Close-up view · the contributor is 18–29, female.
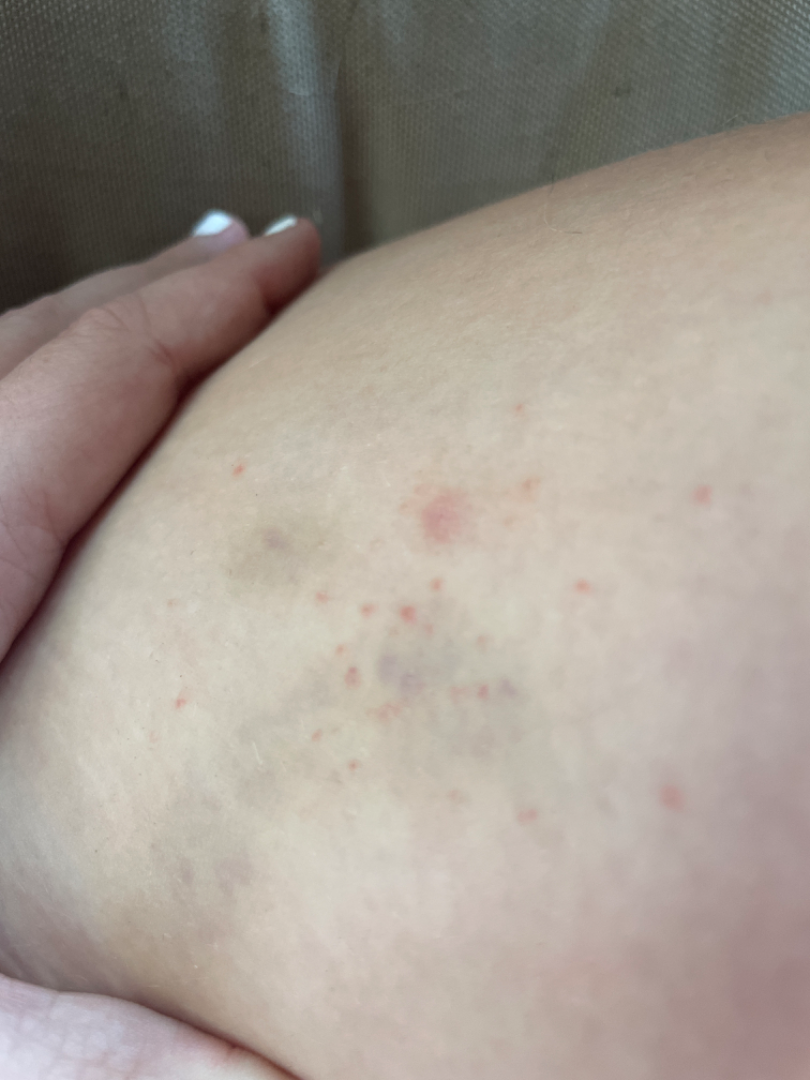Case summary:
– assessment: Folliculitis and Insect Bite were considered with similar weight; less probable is Eczema